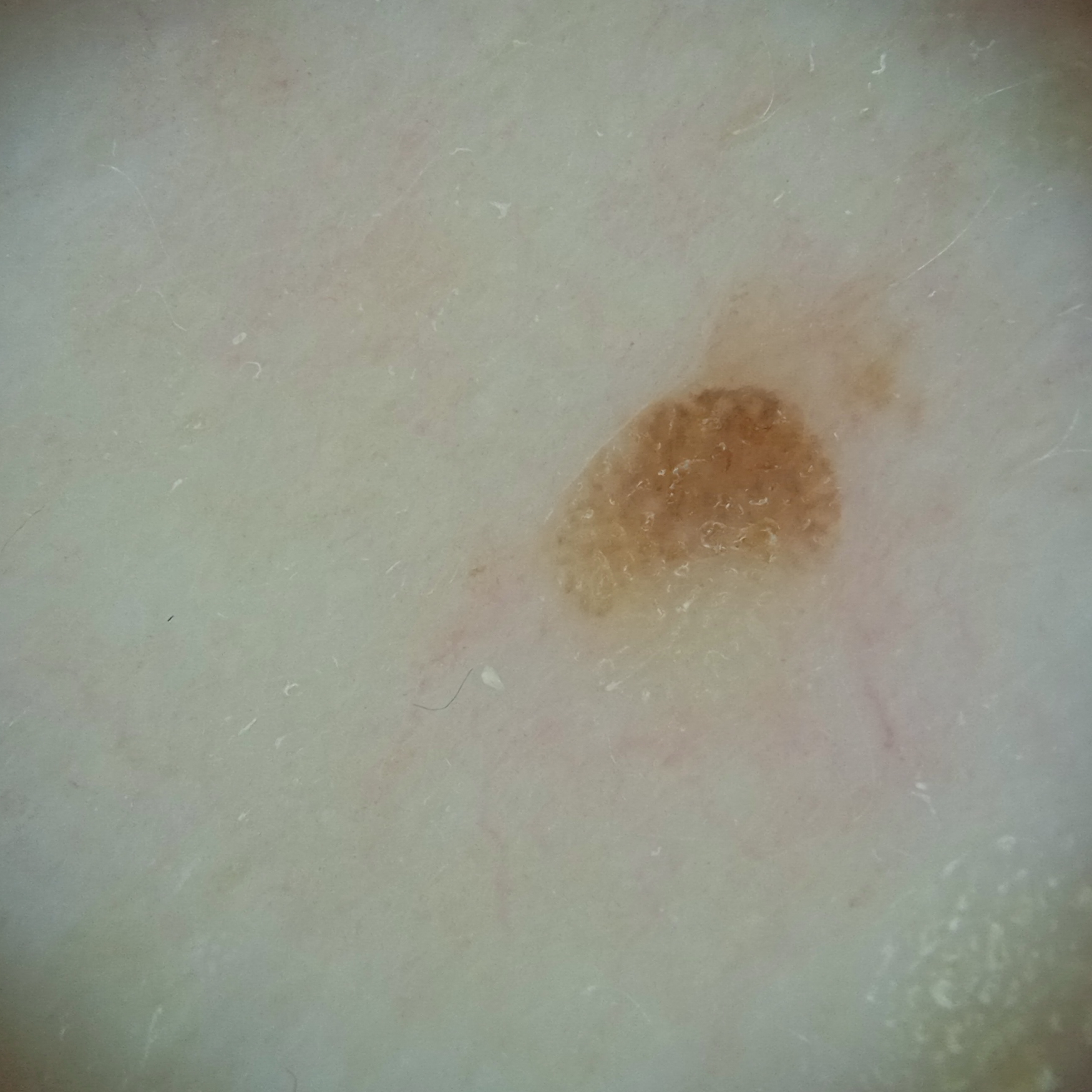nevus count: a moderate number of melanocytic nevi
image: dermoscopy
referral: research study (no referral diagnosis)
sun reaction: skin reddens with sun exposure
risk factors: a personal history of cancer, a personal history of skin cancer
subject: male, aged 77
lesion size: 3 mm
diagnosis: seborrheic keratosis (dermatologist consensus)